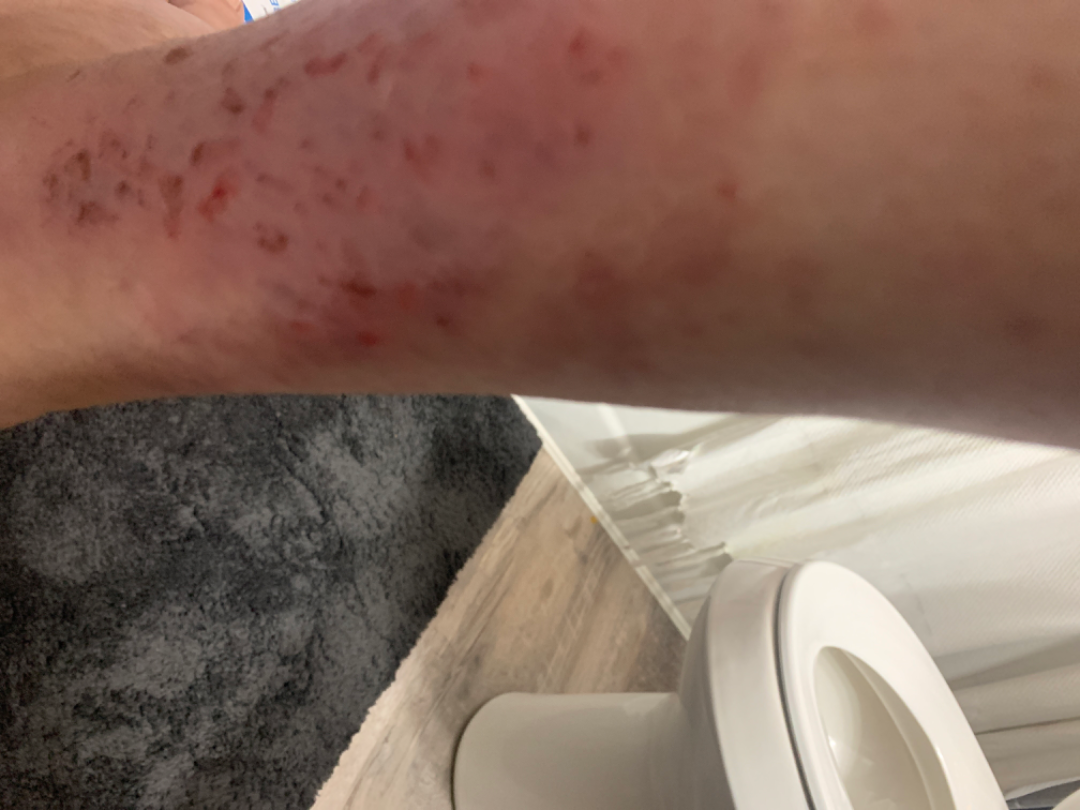assessment: could not be assessed; skin tone: non-clinician graders estimated 2 on the MST; patient: female, age 50–59; other reported symptoms: none reported; patient's own categorization: a rash; reported symptoms: itching, burning and darkening; described texture: flat; view: at an angle; site: leg.